A dermoscopic close-up of a skin lesion.
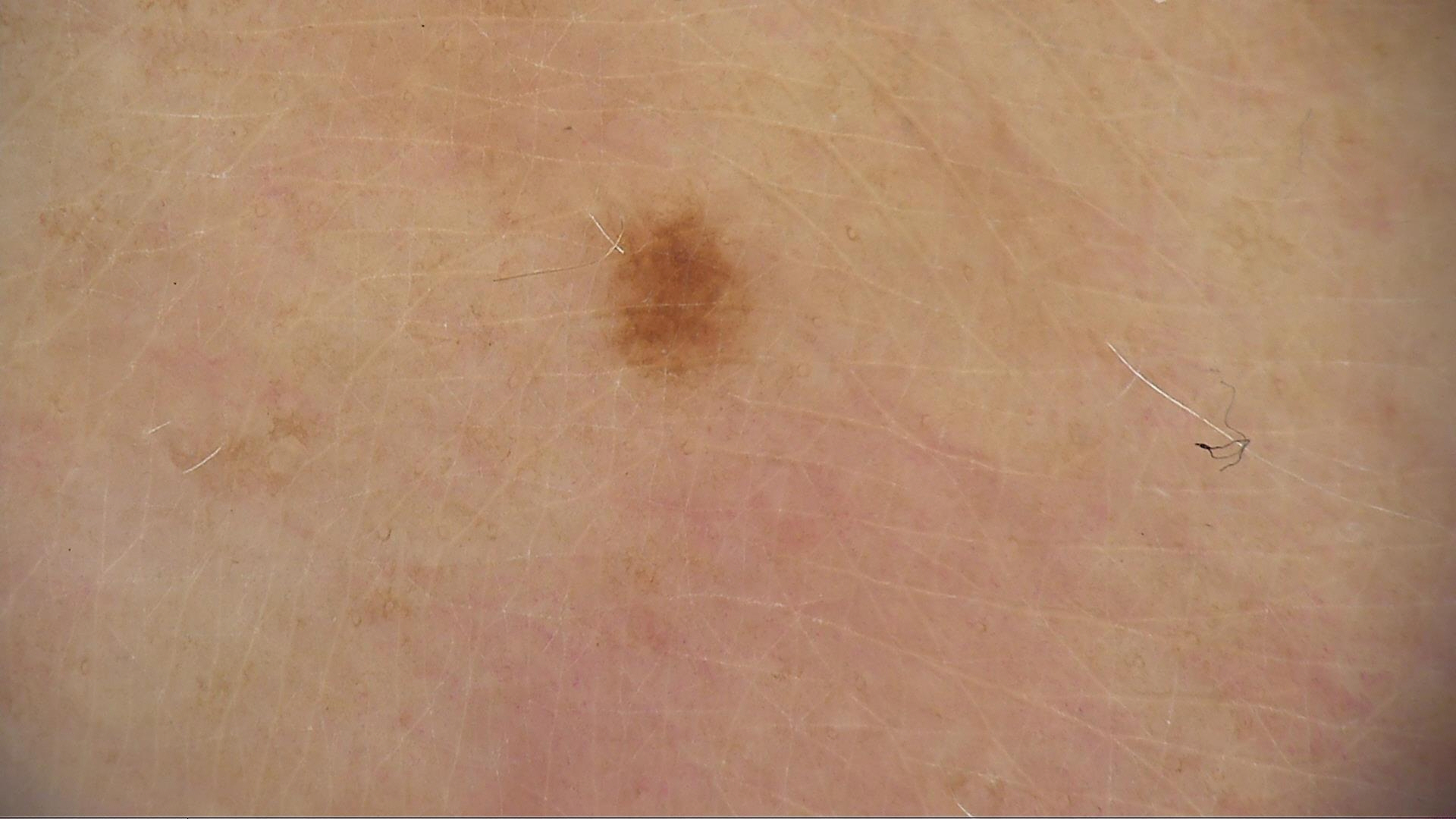| key | value |
|---|---|
| label | dysplastic junctional nevus (expert consensus) |